A skin lesion imaged with a dermatoscope, a female subject aged approximately 65 — 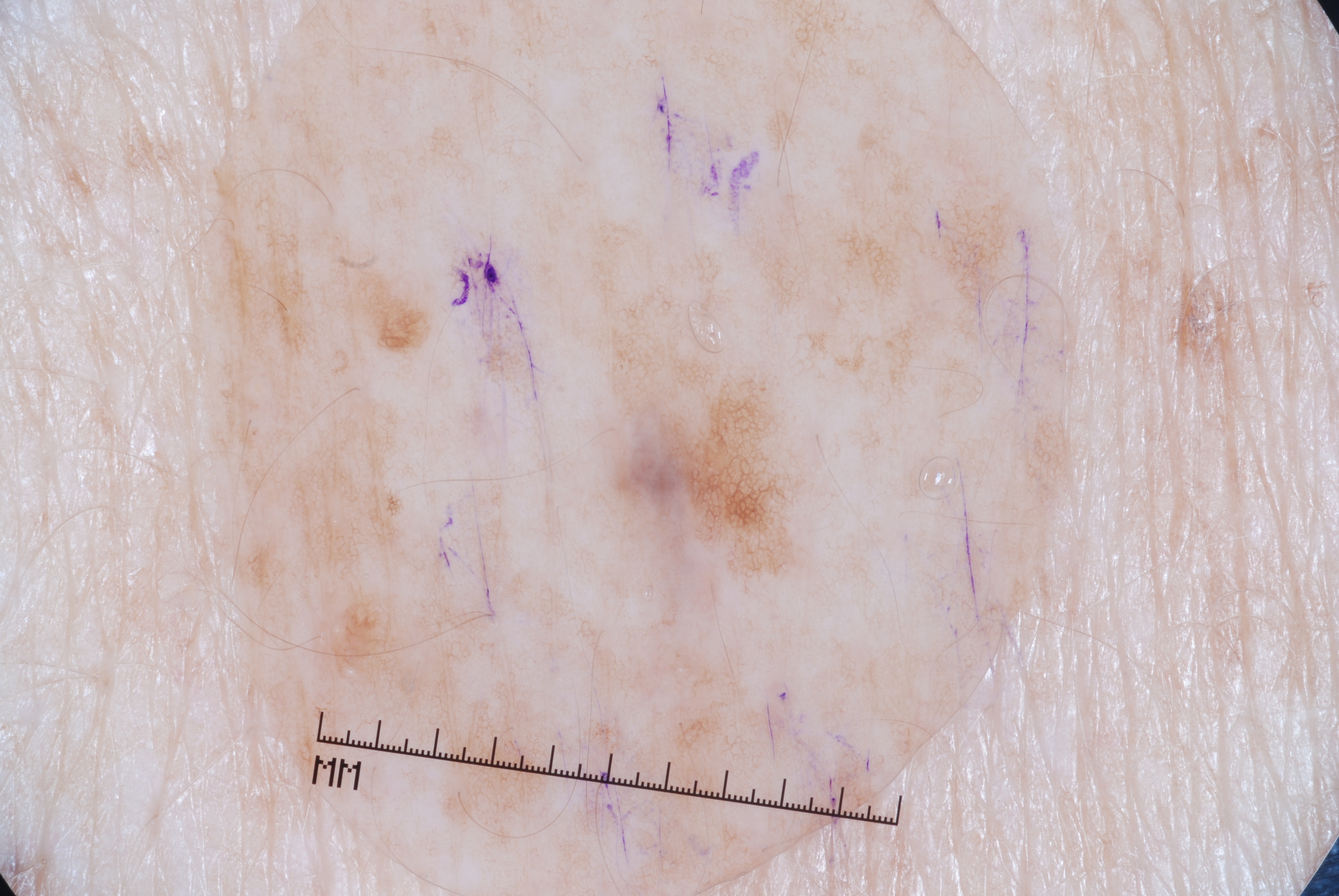lesion location = 553, 201, 844, 610 | extent = small | dermoscopic findings = pigment network; absent: milia-like cysts, streaks, and negative network | assessment = a melanocytic nevus.